The subject is a female aged 30–39 · a close-up photograph · located on the head or neck:
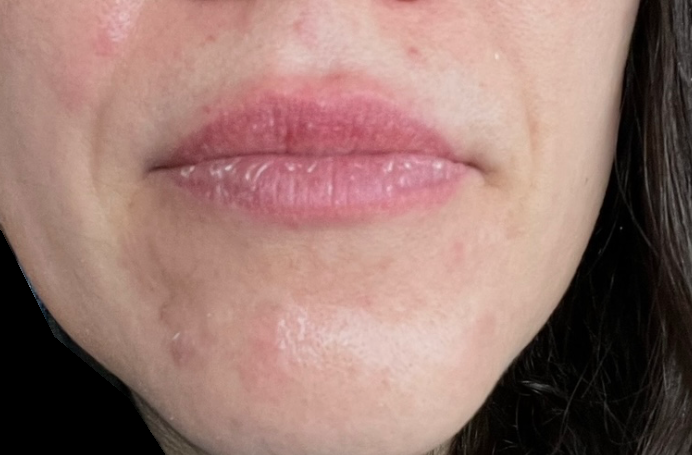surface texture: rough or flaky, raised or bumpy and fluid-filled | onset: one to three months | other reported symptoms: none reported | skin tone: human graders estimated 2 on the Monk Skin Tone | reported symptoms: enlargement, bothersome appearance and pain | patient's own categorization: acne | impression: Perioral Dermatitis (54%); Acne (23%); Rosacea (23%).